The patient says their skin tans without first burning · acquired for a research image collection, with no referral diagnosis · a female subject 47 years of age · a skin lesion imaged with a dermatoscope · a moderate number of moles by the patient's own estimate:
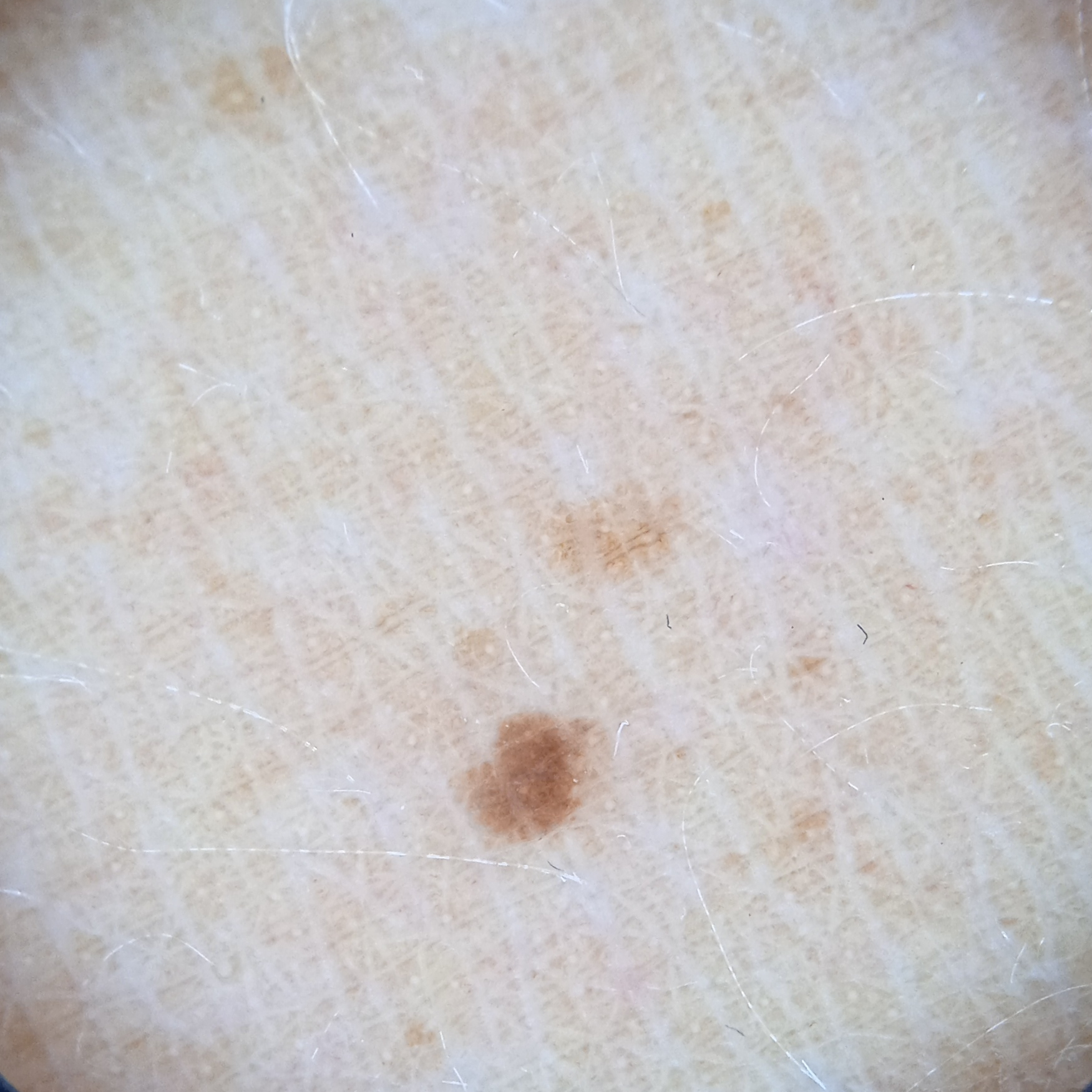– location: the back
– diagnostic label: melanocytic nevus (dermatologist consensus)